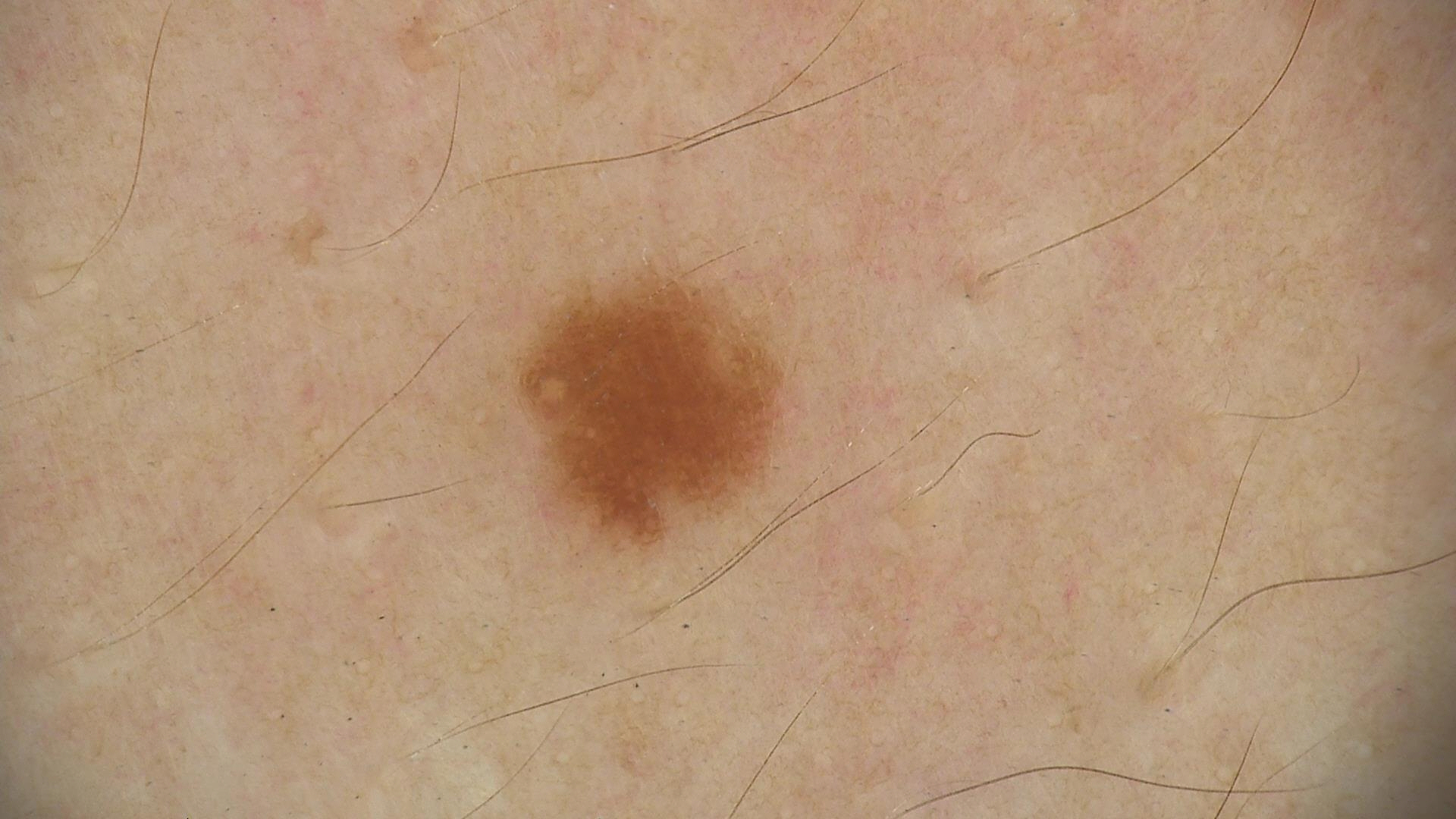Q: What was the diagnostic impression?
A: dysplastic junctional nevus (expert consensus)